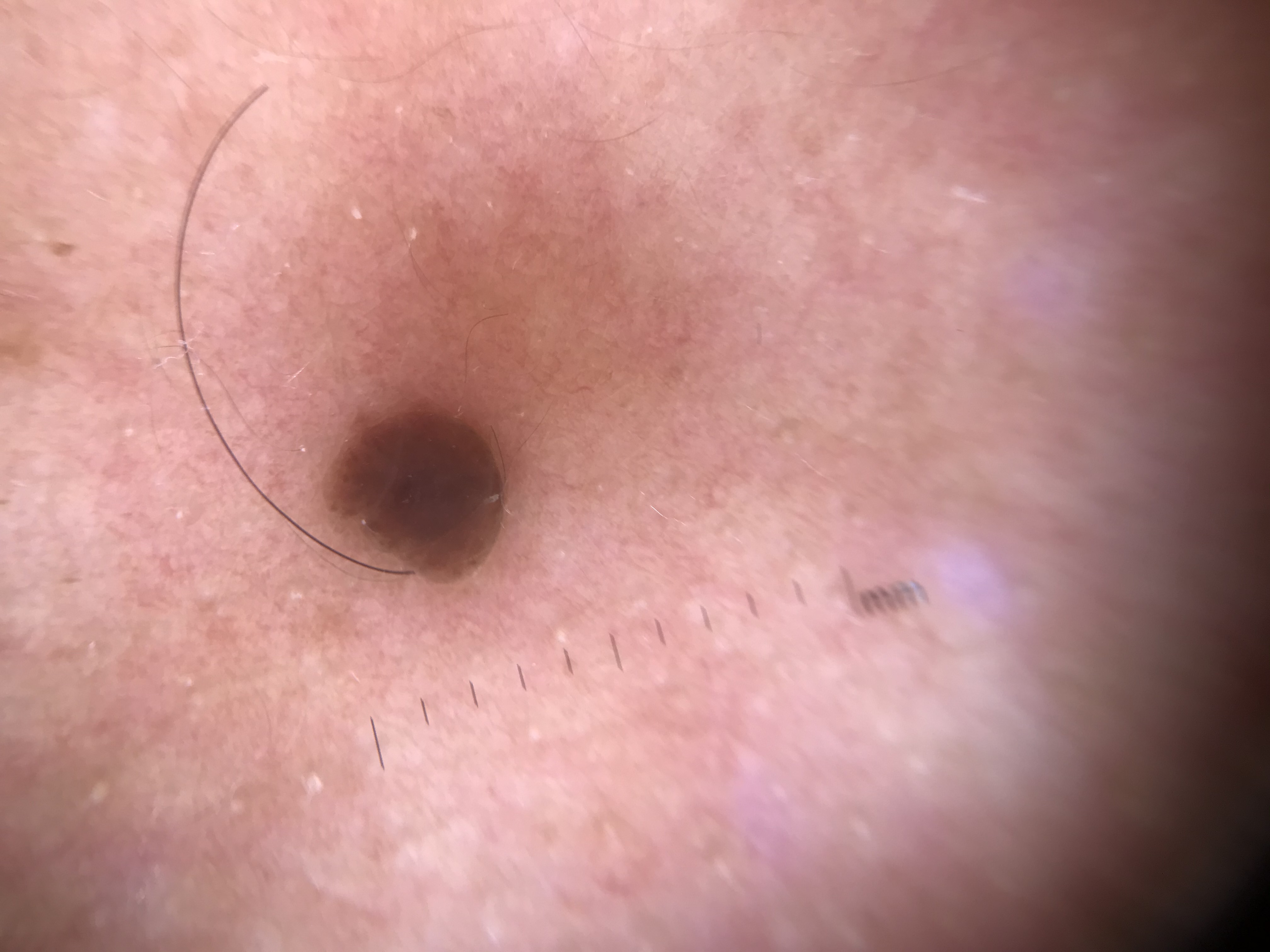image type: dermatoscopy | lesion type: banal | diagnosis: compound nevus (expert consensus).